Collected as part of a research study, without a referral diagnosis. Dermoscopy of a skin lesion. The patient describes having few moles overall. A female subject age 67. The patient says their skin tans without first burning — 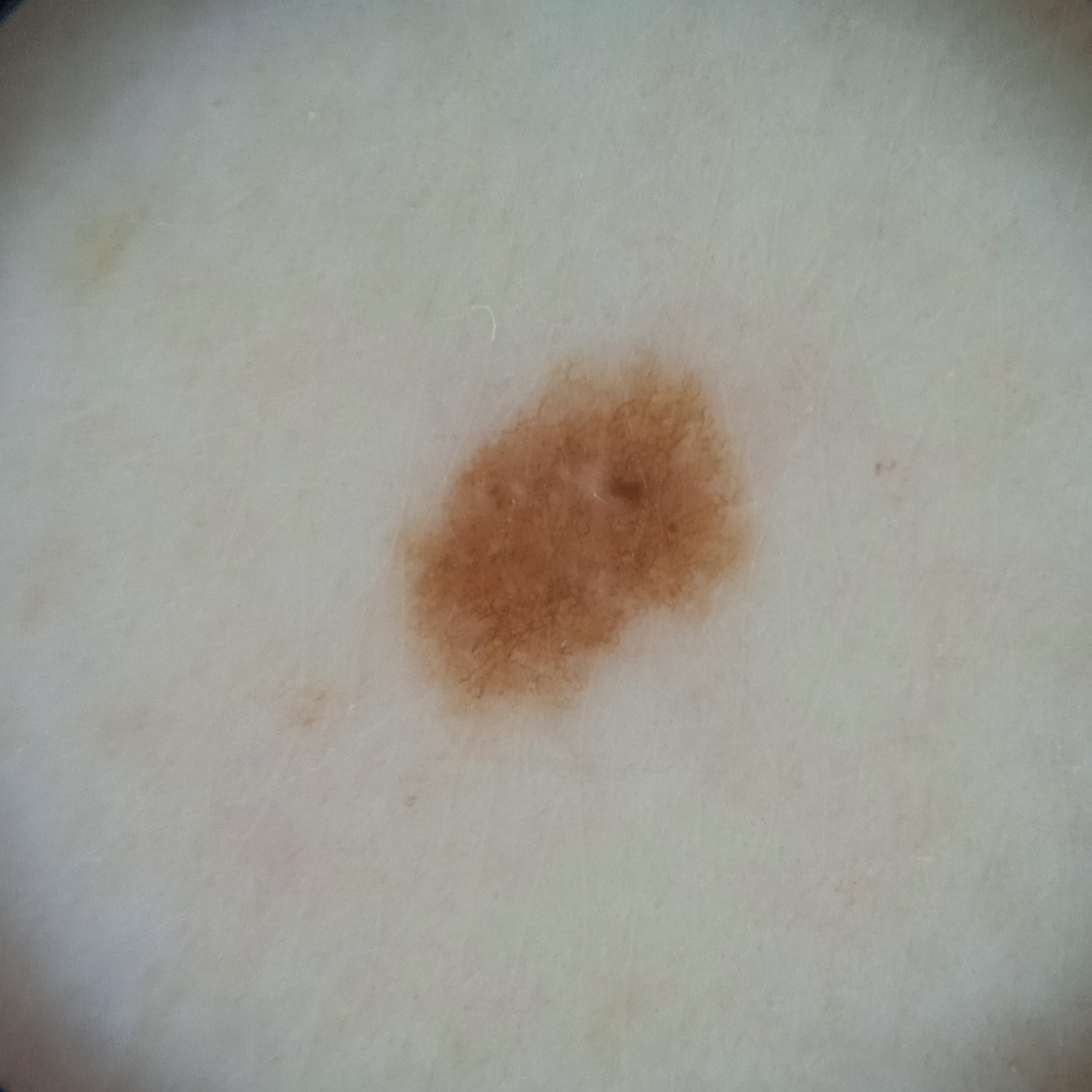Findings: Located on an arm. The lesion is about 4.9 mm across. Conclusion: The four-dermatologist consensus diagnosis was a melanocytic nevus; diagnostic confidence was good; reviewers noted it may also be a melanoma.